The photograph was taken at a distance. Male patient, age 18–29:
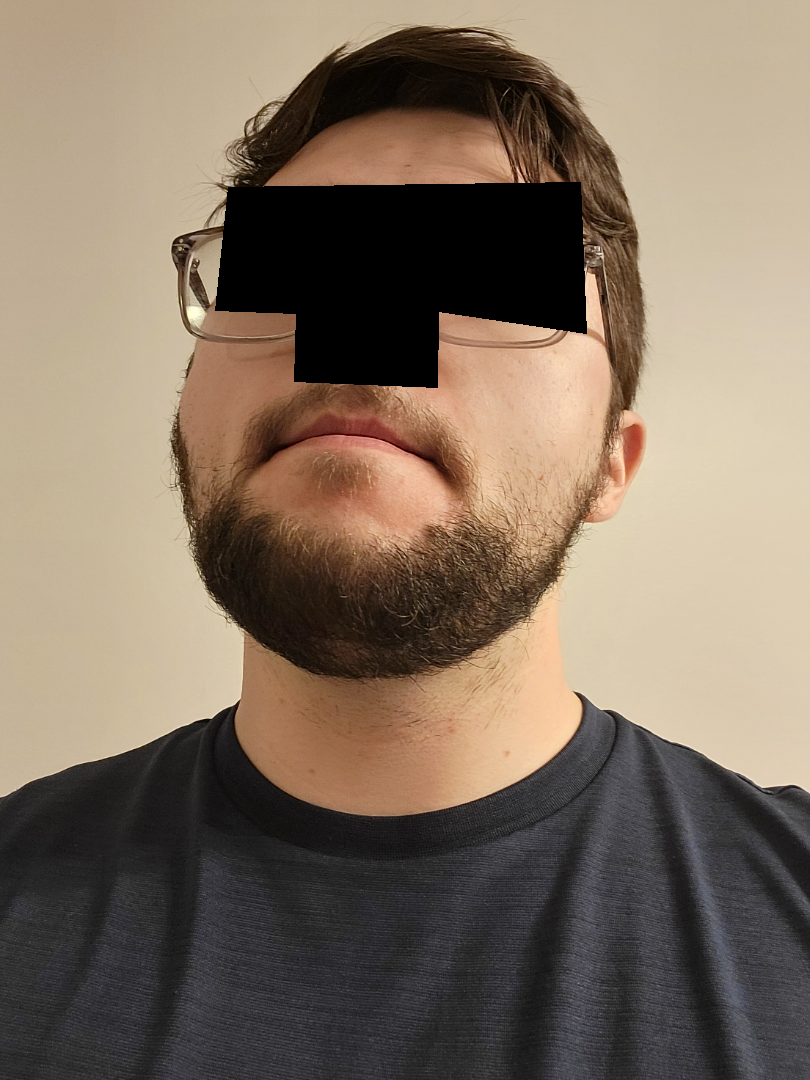Impression: The impression on review was Seborrheic Dermatitis.